The patient is a female aged 50–59; self-categorized by the patient as skin that appeared healthy to them; the contributor reports burning, itching and pain; located on the leg; the photo was captured at a distance; the contributor reports the lesion is flat; present for one to four weeks: 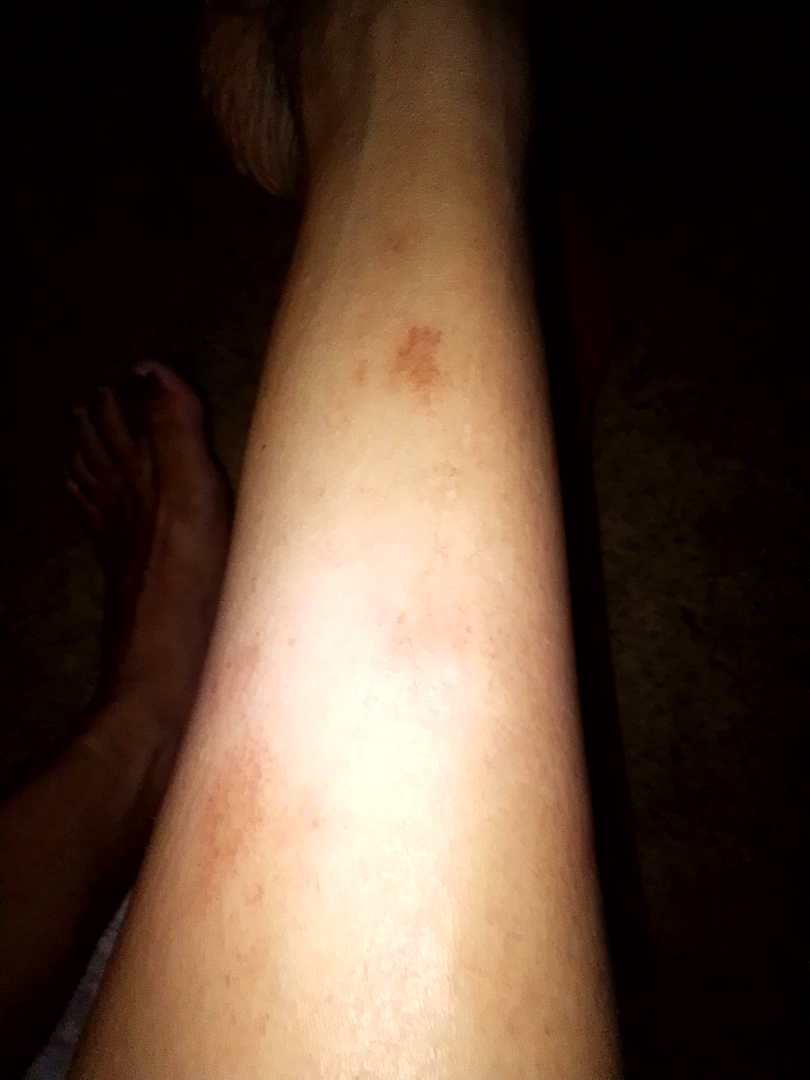On photographic review, most consistent with Pigmented purpuric eruption.